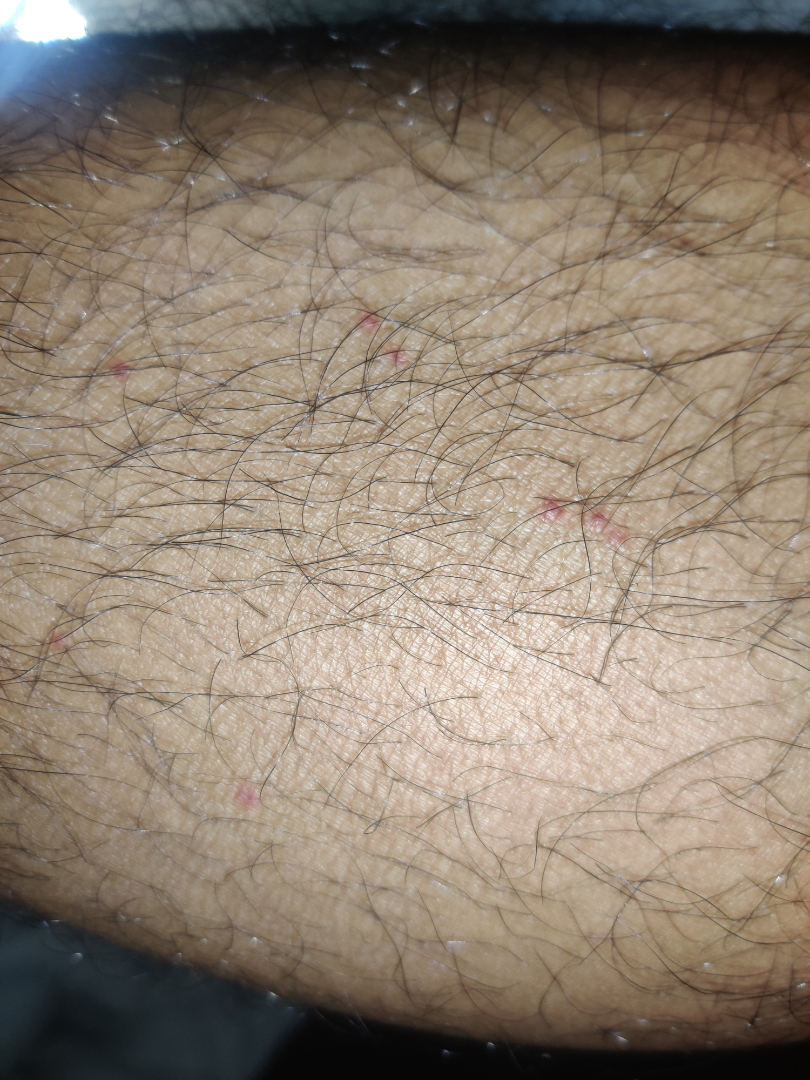assessment — unable to determine.